The patient considered this a rash · present for one to four weeks · the lesion is associated with itching · the patient is a female aged 18–29 · Fitzpatrick III; non-clinician graders estimated Monk Skin Tone 3 · the lesion involves the back of the torso and front of the torso · a close-up photograph — 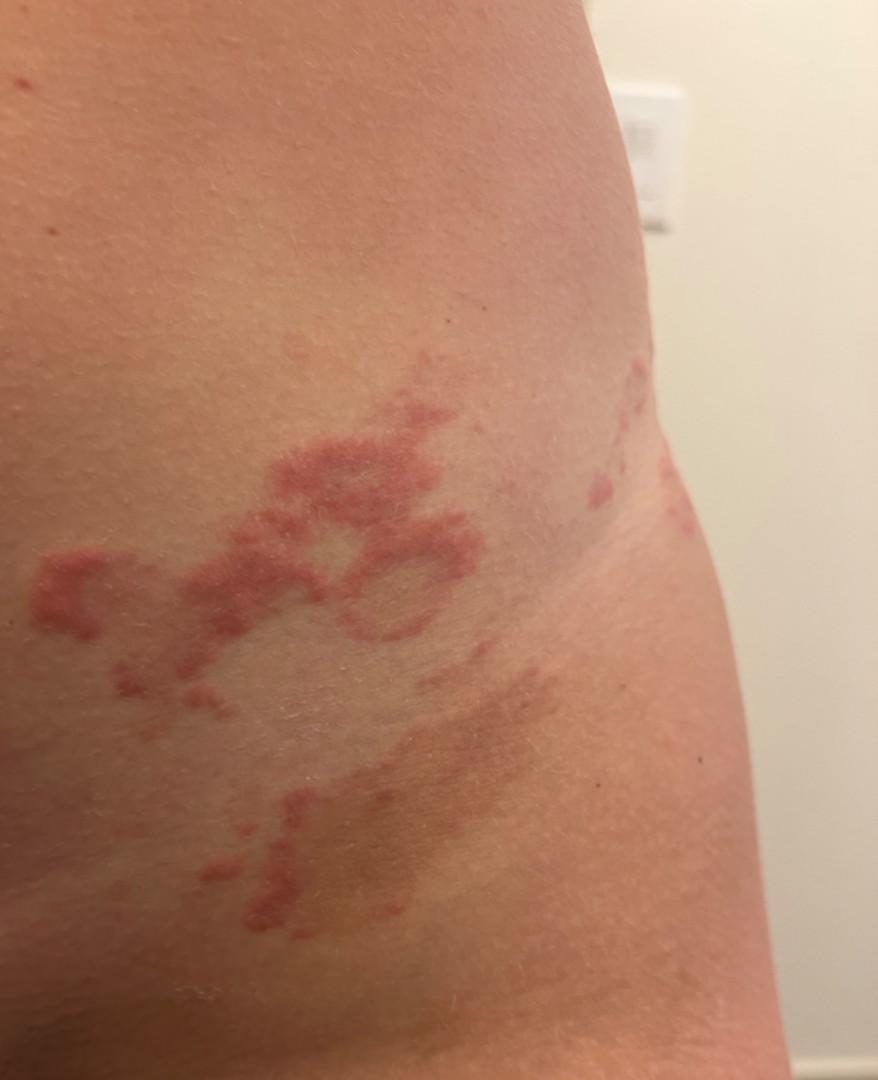Assessment:
Granuloma annulare, Pemphigoid gestationis and Pruritic urticarial papules and plaques of pregnancy were each considered, in no particular order.